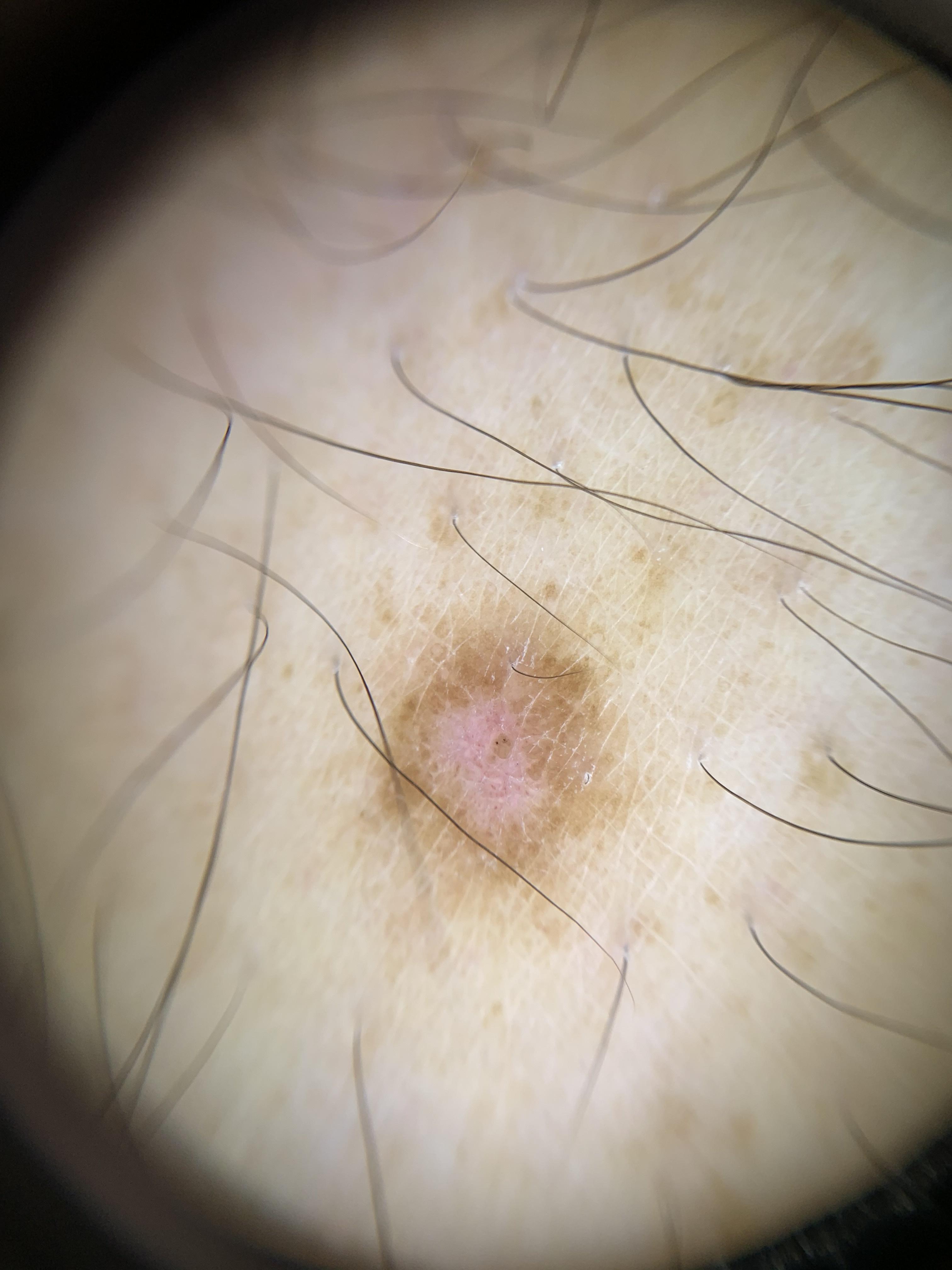Q: Who is the patient?
A: male, aged 43 to 47
Q: How was this image acquired?
A: dermoscopy
Q: Where on the body is the lesion?
A: a lower extremity
Q: What was the clinical impression?
A: Dermatofibroma